A skin lesion imaged with a dermatoscope.
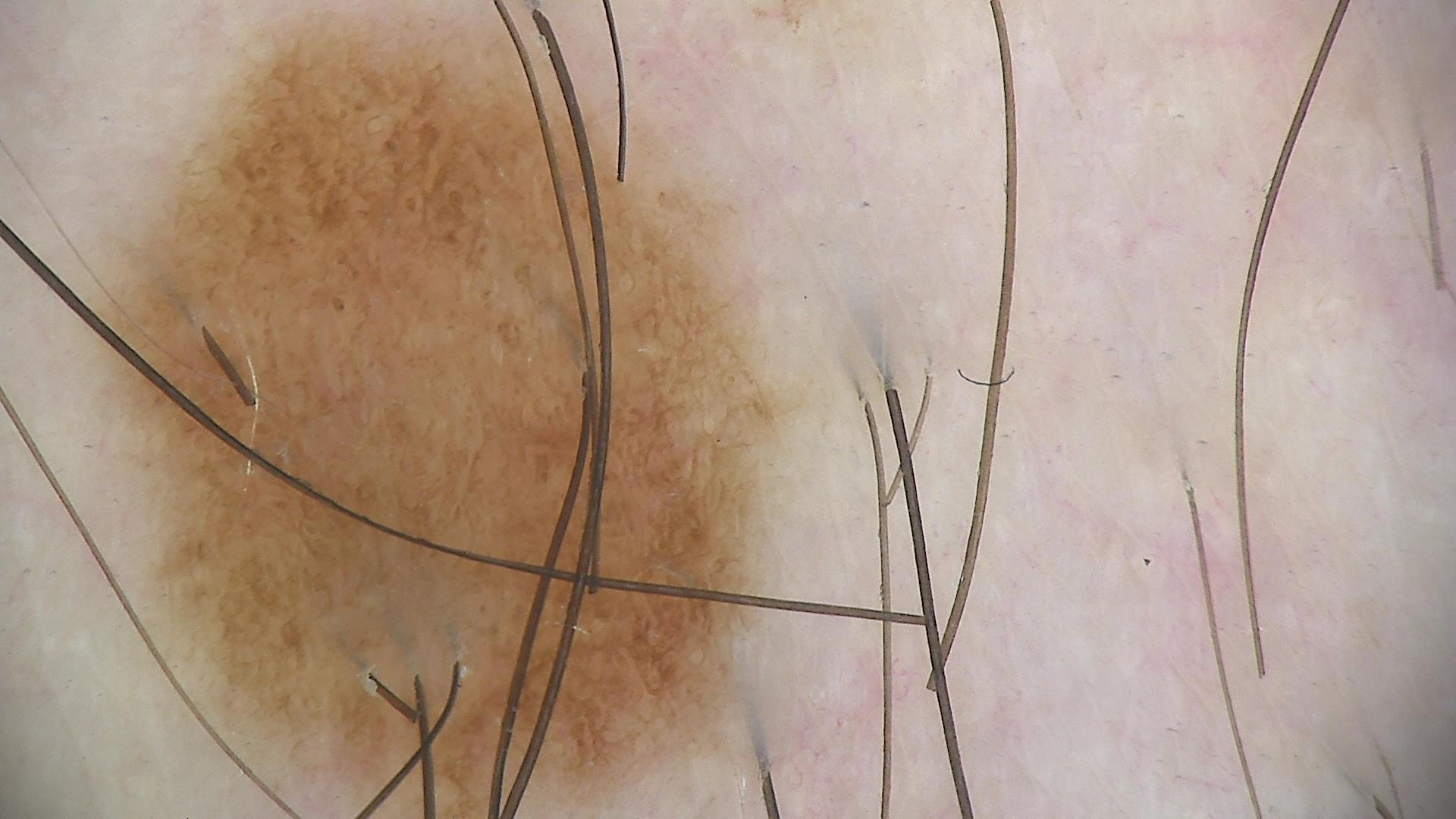* assessment — dysplastic junctional nevus (expert consensus)